A dermatoscopic image of a skin lesion:
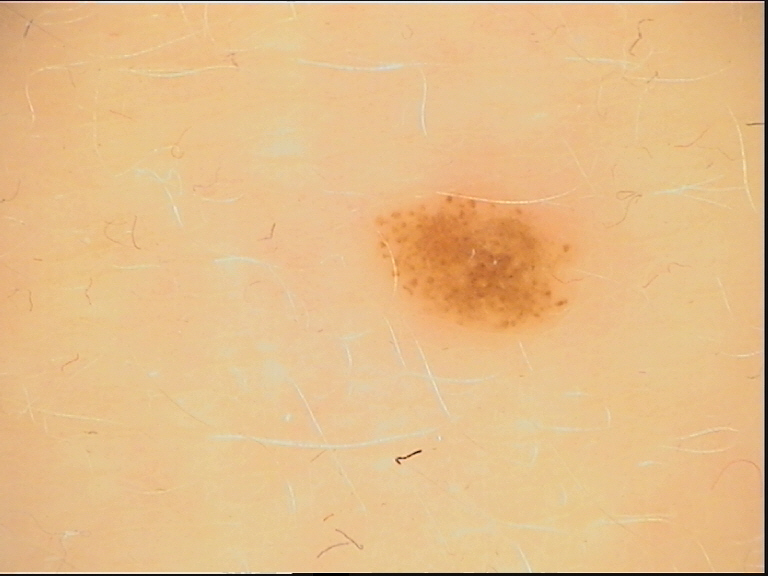assessment=dysplastic junctional nevus (expert consensus)